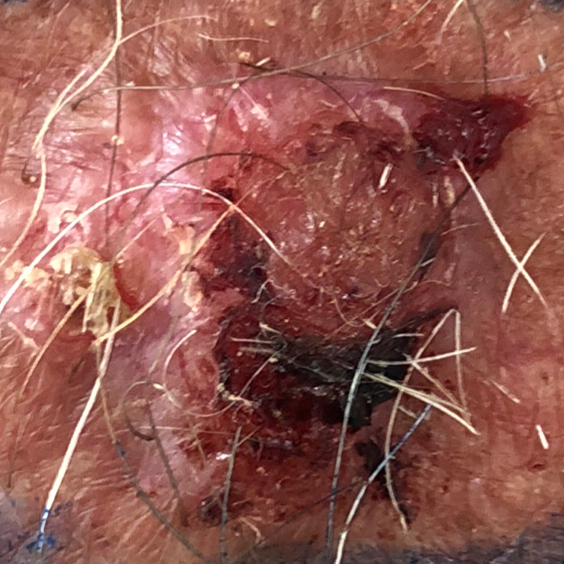subject: male, aged 58
location: the chest
reported symptoms: elevation, bleeding, itching, pain, growth / no change in appearance
pathology: basal cell carcinoma (biopsy-proven)